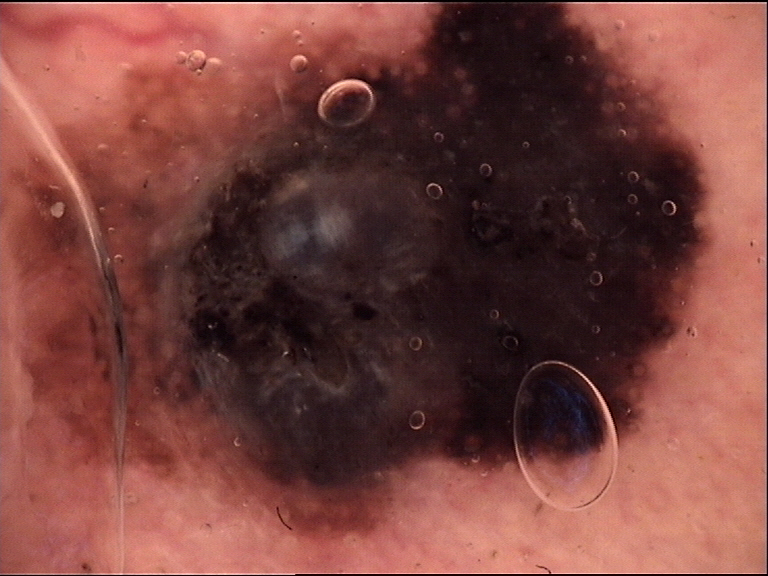image: dermatoscopy
diagnostic label: melanoma (biopsy-proven)